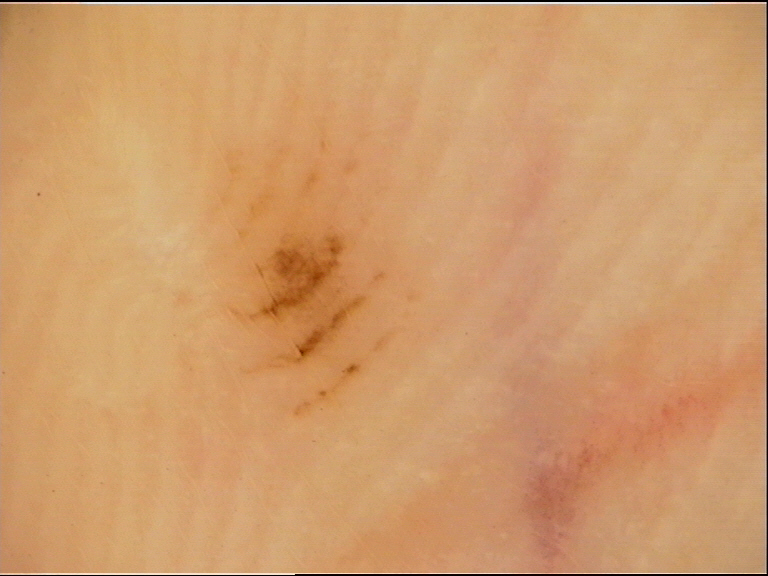imaging: dermoscopy | label: acral junctional nevus (expert consensus).